Collected as part of a research study, without a referral diagnosis. The patient says their skin tans without first burning. A moderate number of moles by the patient's own estimate. By self-report, a history of sunbed use.
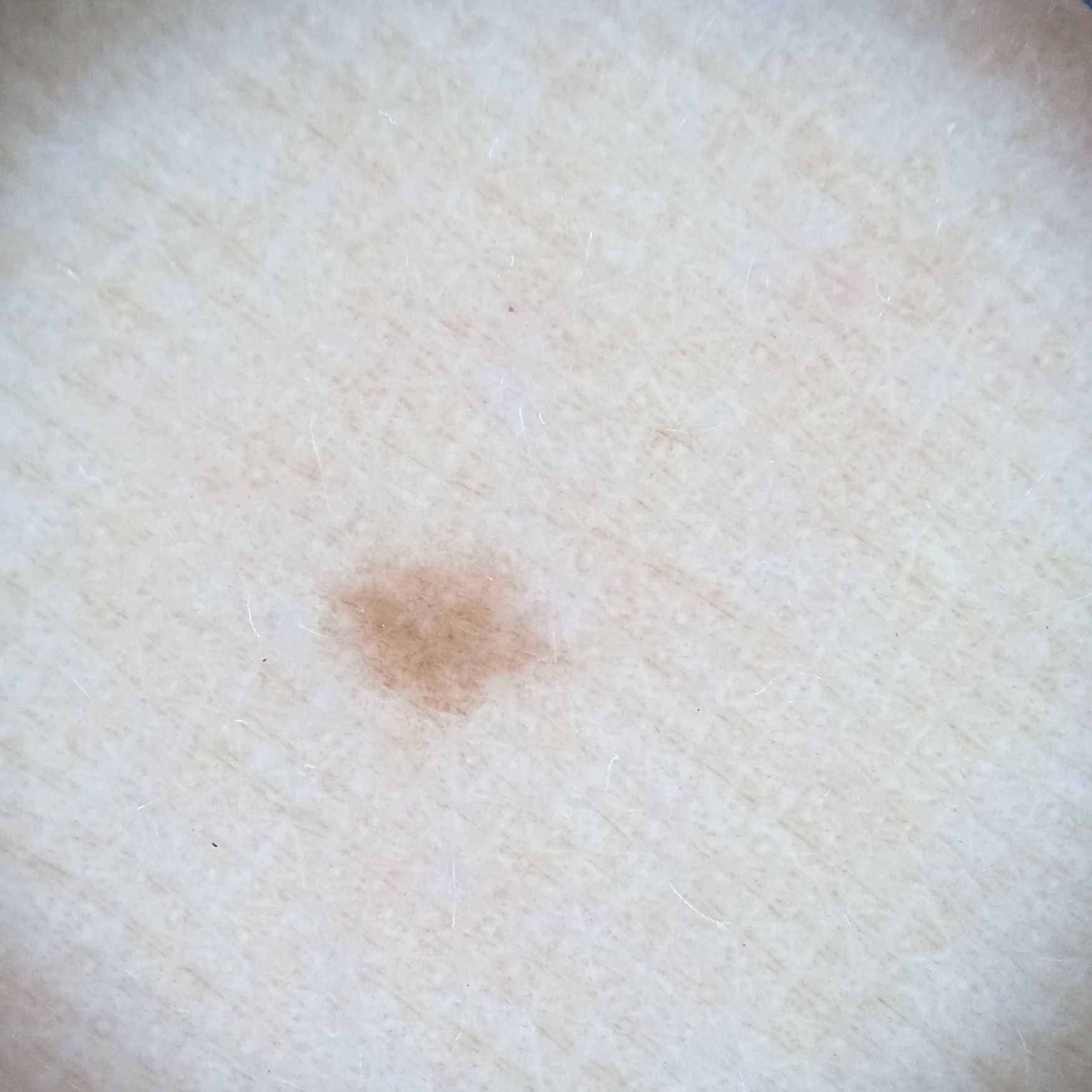{
  "lesion_location": "an arm",
  "diagnosis": {
    "name": "melanocytic nevus",
    "malignancy": "benign"
  }
}